A skin lesion imaged with contact-polarized dermoscopy. A female patient about 65 years old. Recorded as FST II.
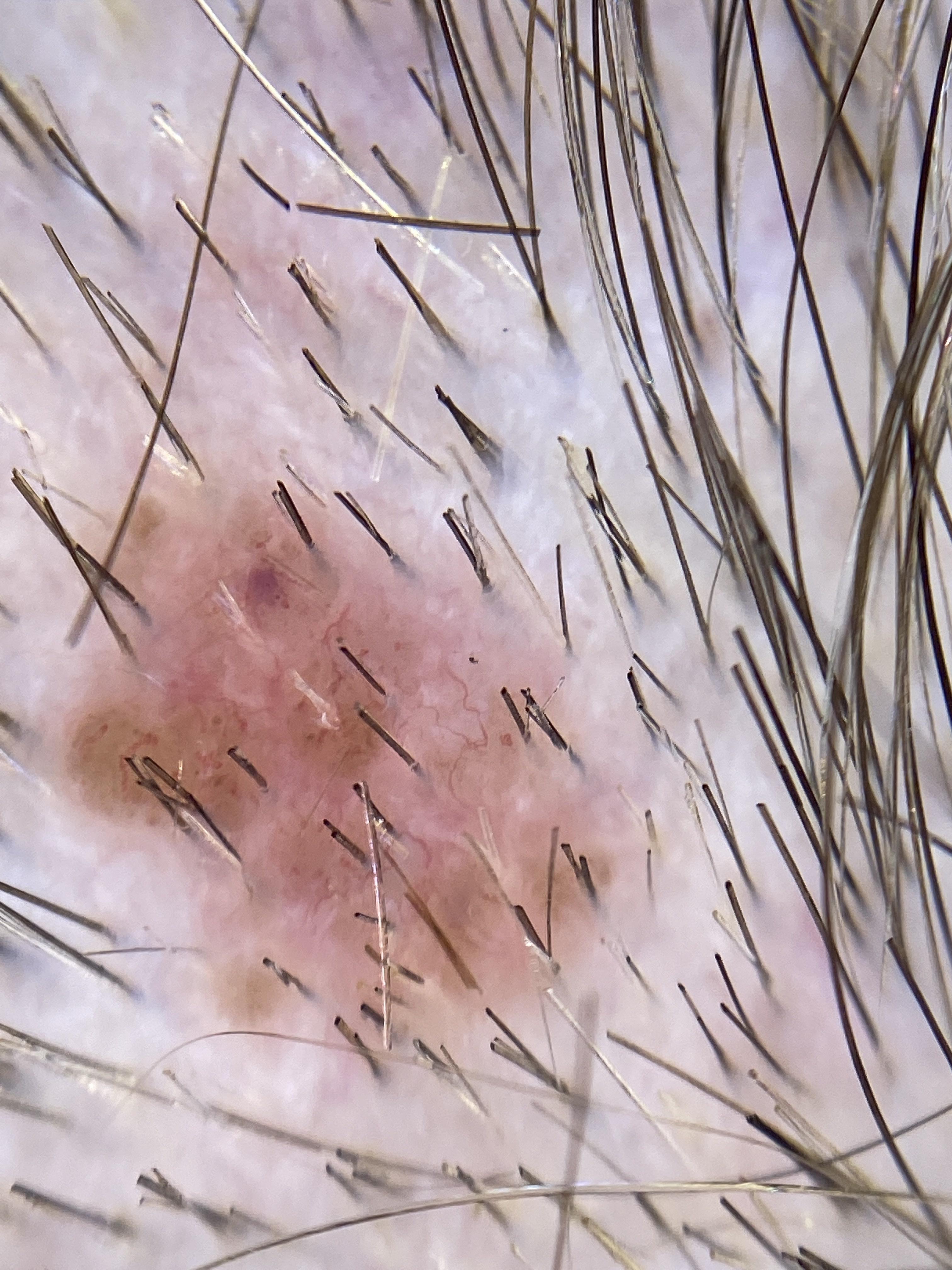Q: Where on the body is the lesion?
A: the head or neck
Q: What did the workup show?
A: Basal cell carcinoma (biopsy-proven)